The photo was captured at a distance. The condition has been present for one to three months. Reported lesion symptoms include enlargement, darkening and itching. Texture is reported as raised or bumpy. The patient described the issue as a rash. No constitutional symptoms were reported. Located on the back of the torso. Fitzpatrick phototype III; human graders estimated MST 2 or 3. The patient is 18–29, female:
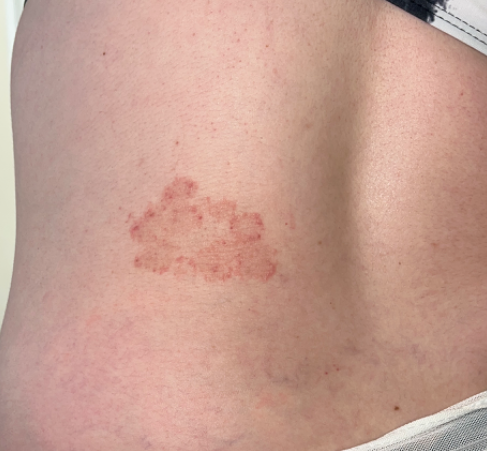The reviewing dermatologist's impression was: most consistent with Tinea.